The lesion is associated with itching, the photograph is a close-up of the affected area, self-categorized by the patient as a rash, present for about one day, the contributor notes the lesion is raised or bumpy — 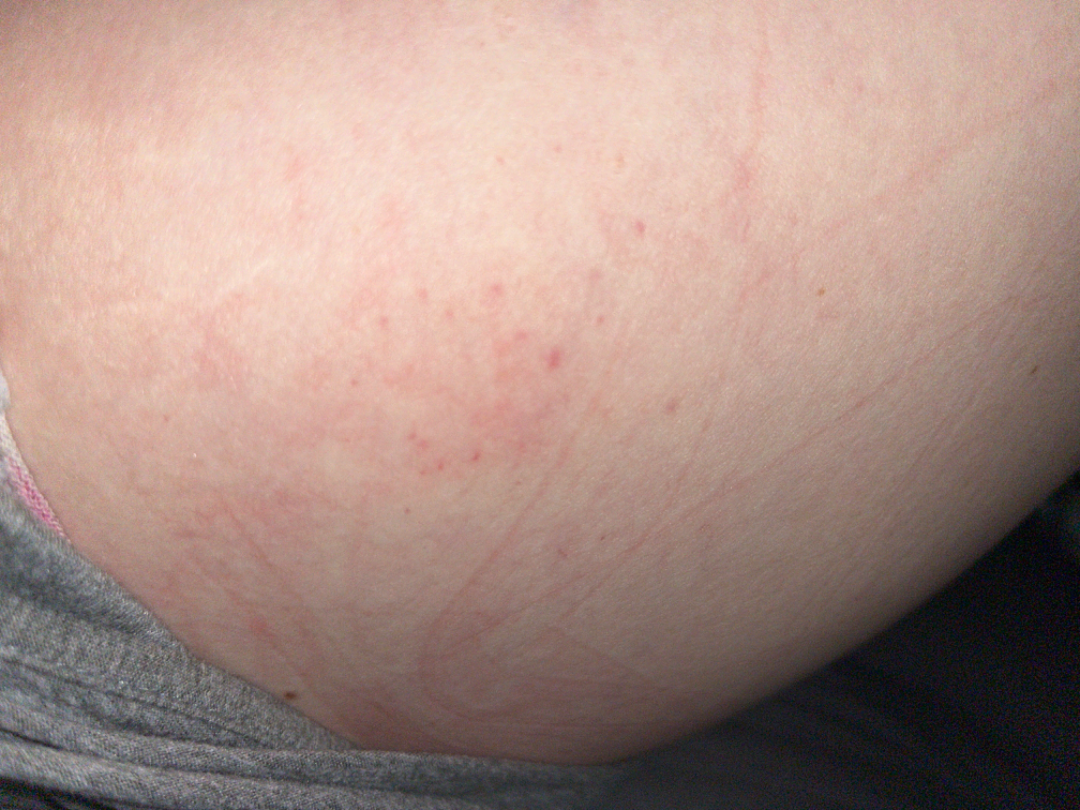Q: What is the differential diagnosis?
A: most likely petechiae